A dermatoscopic image of a skin lesion.
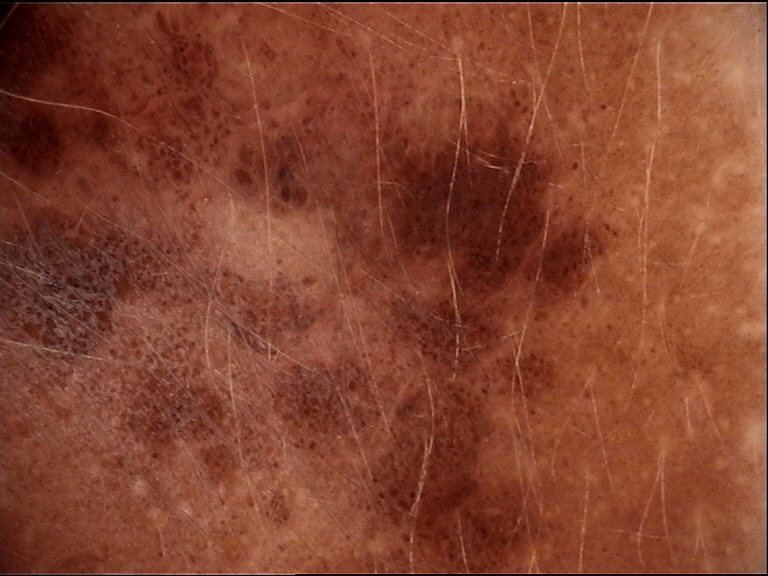The morphology is that of a banal lesion.
Labeled as a congenital junctional nevus.